No relevant systemic symptoms · the affected area is the leg · the contributor notes the lesion is raised or bumpy · self-categorized by the patient as a rash · an image taken at a distance · skin tone: Fitzpatrick phototype II; human graders estimated a MST of 2 · present for less than one week · reported lesion symptoms include itching, enlargement and bothersome appearance — 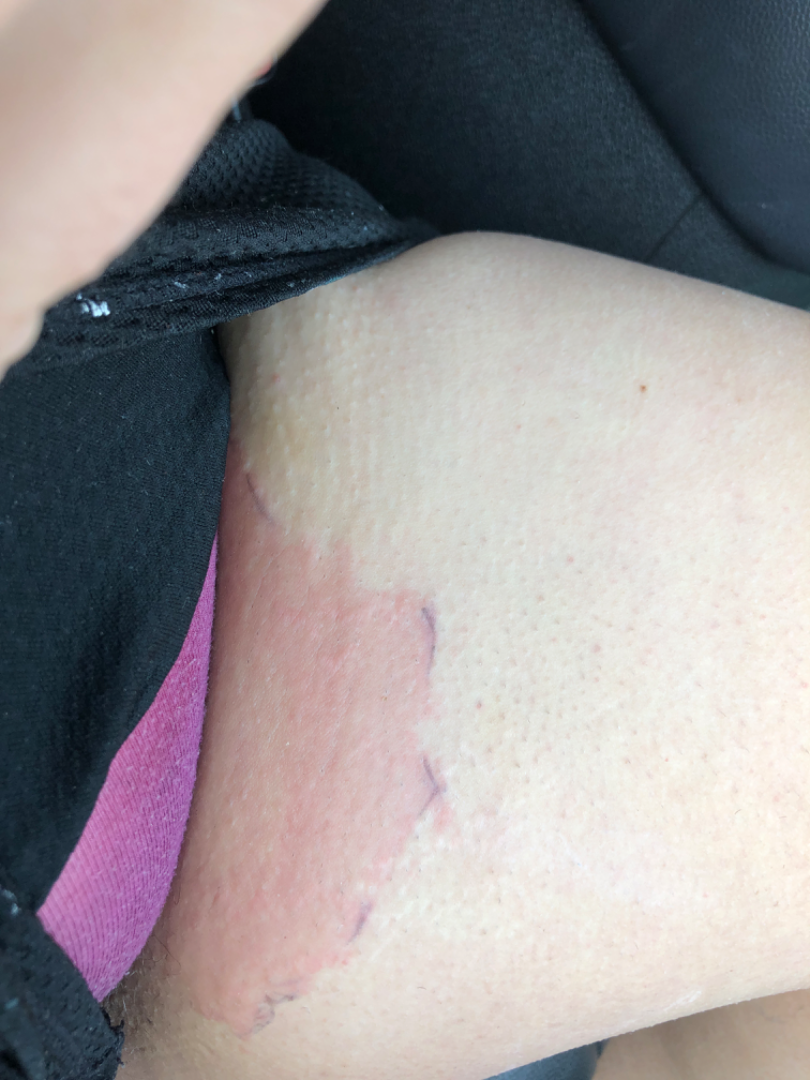differential:
  - Cellulitis
  - Intertrigo
  - Psoriasis